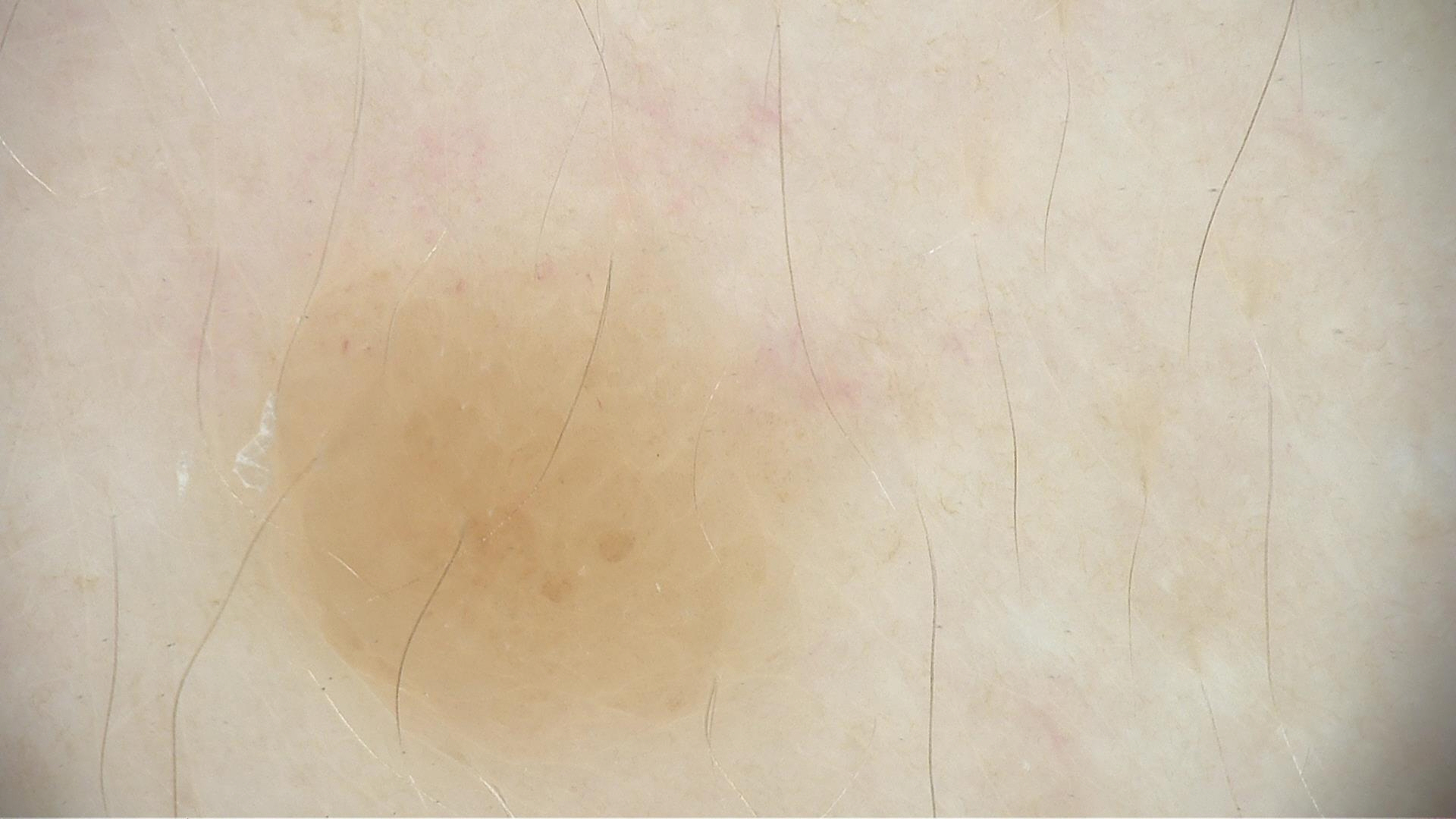assessment = dermal nevus (expert consensus).